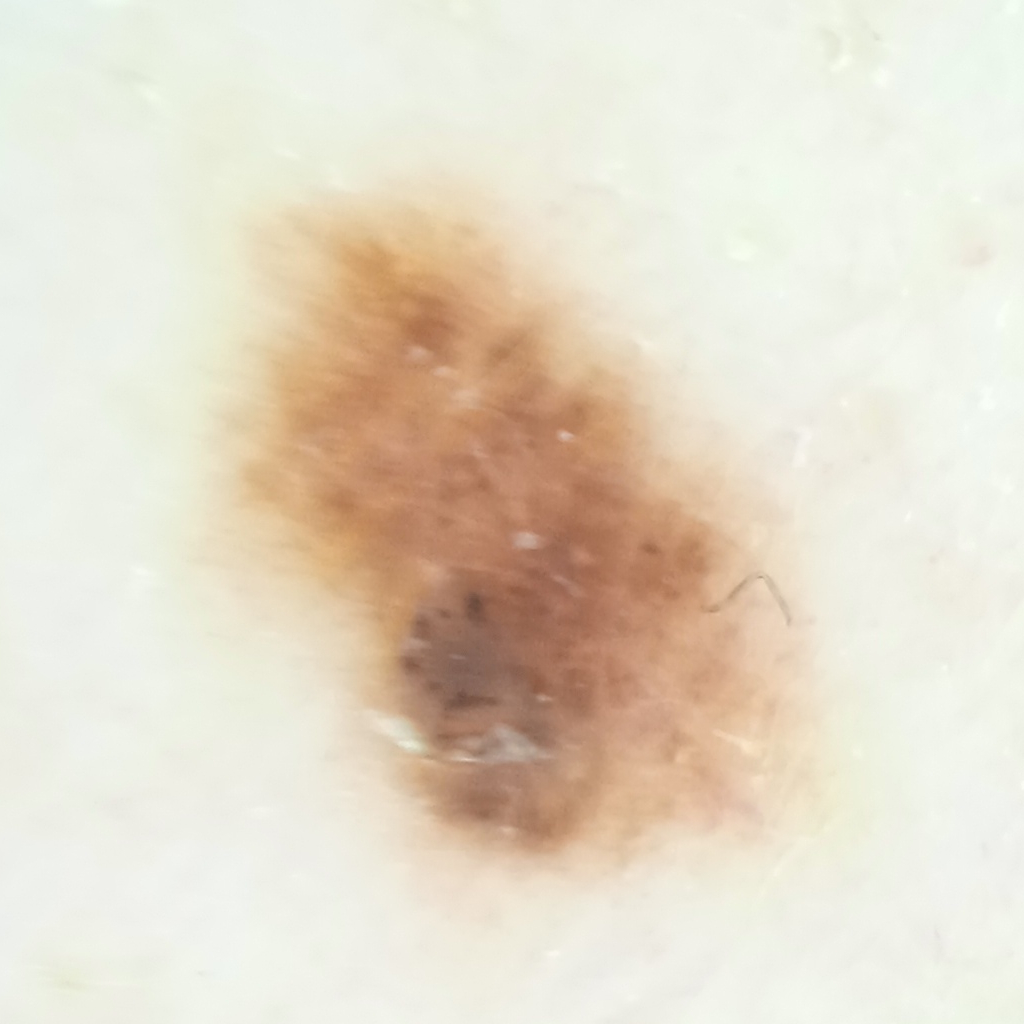diagnosis = melanocytic nevus (biopsy-proven)